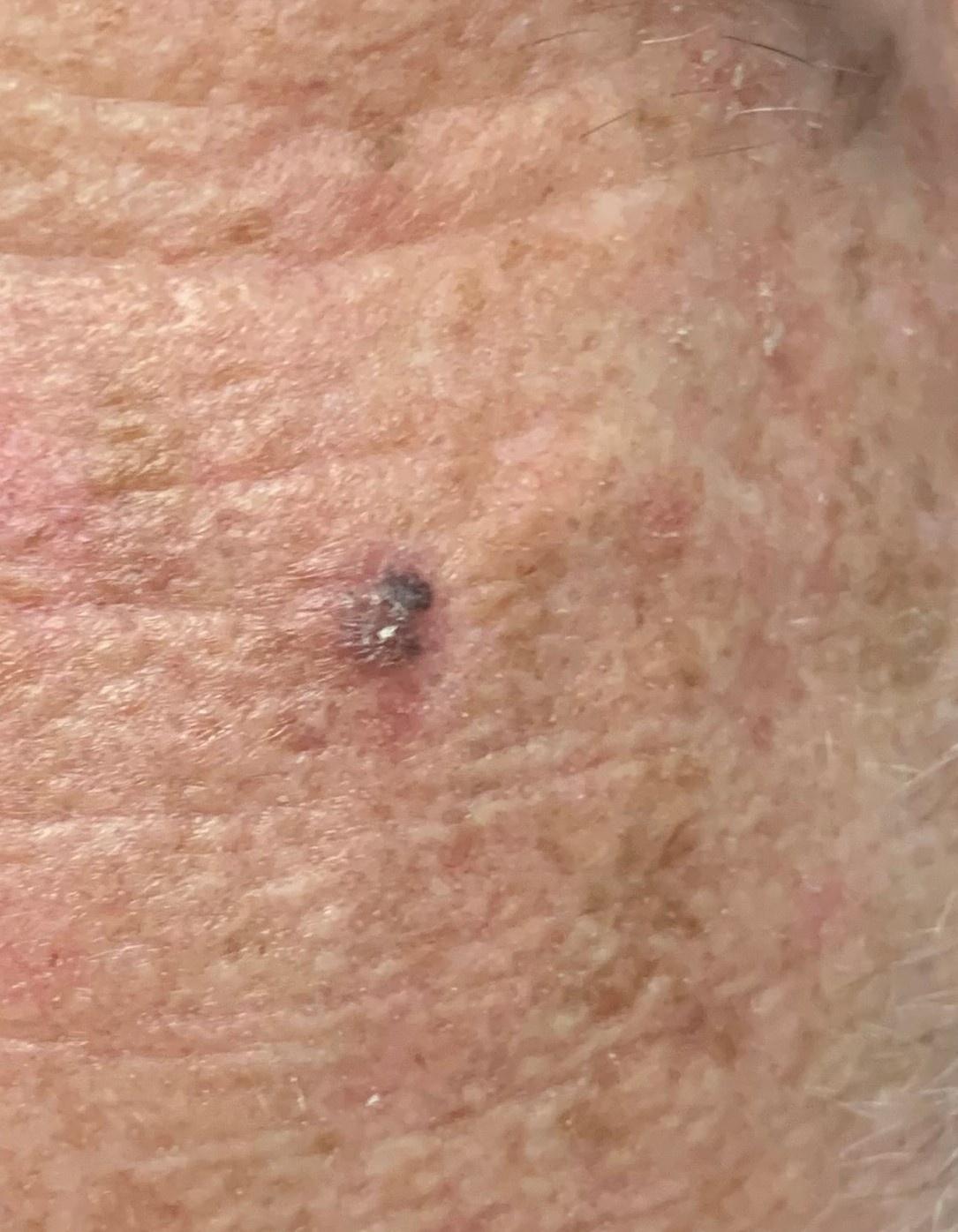Q: What Fitzpatrick skin type was recorded?
A: II
Q: What kind of image is this?
A: clinical overview photograph
Q: What is the melanoma history?
A: a prior melanoma but no melanoma in first-degree relatives
Q: What are the patient's age and sex?
A: male, about 80 years old
Q: What did the workup show?
A: Seborrheic keratosis (biopsy-proven)